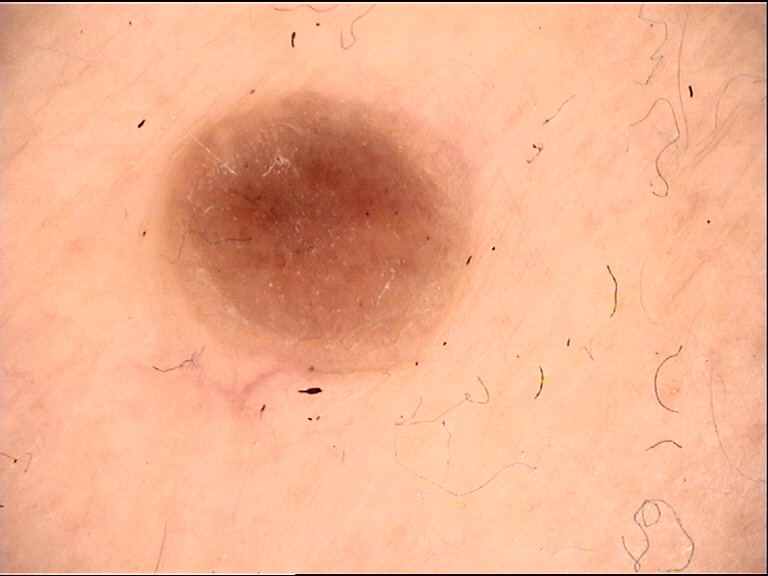The diagnosis was a seborrheic keratosis.